Texture is reported as raised or bumpy; the lesion involves the leg; the contributor is 18–29, female; reported lesion symptoms include itching and bothersome appearance; the photograph was taken at an angle.
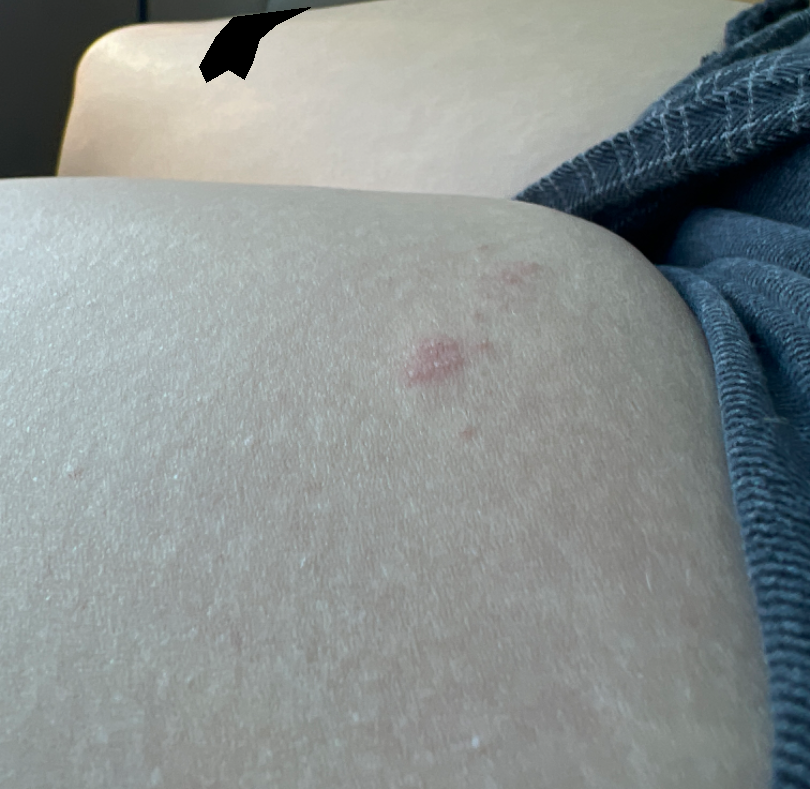Review:
Folliculitis, Allergic Contact Dermatitis and Herpes Simplex were each considered, in no particular order.